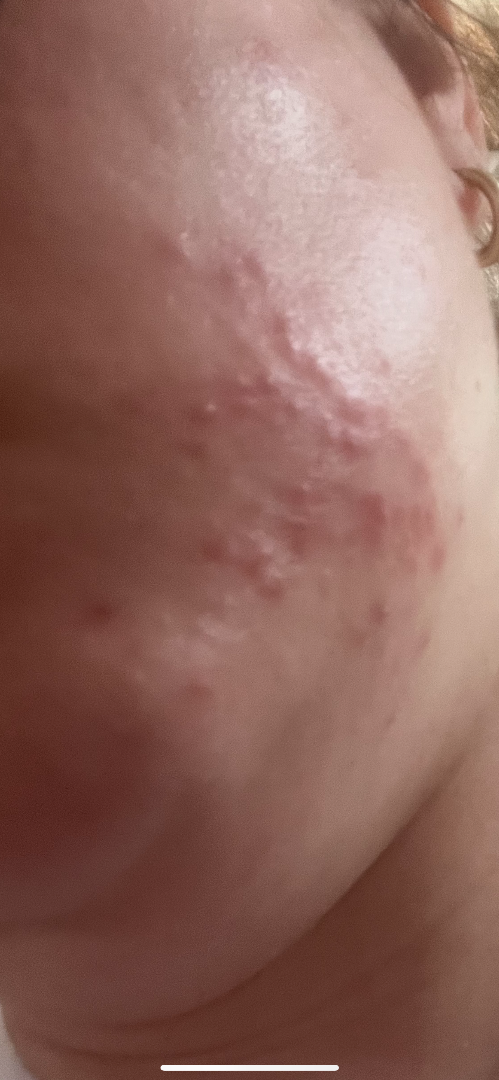Patient information:
Fitzpatrick III; human graders estimated Monk Skin Tone 1 or 2. An image taken at an angle. Reported duration is one to four weeks. The lesion is described as fluid-filled and raised or bumpy. The patient considered this a rash. Female contributor, age 30–39. The patient also reports mouth sores.
Review:
Acne (possible); Rosacea (possible).